The arm is involved; the photo was captured at a distance:
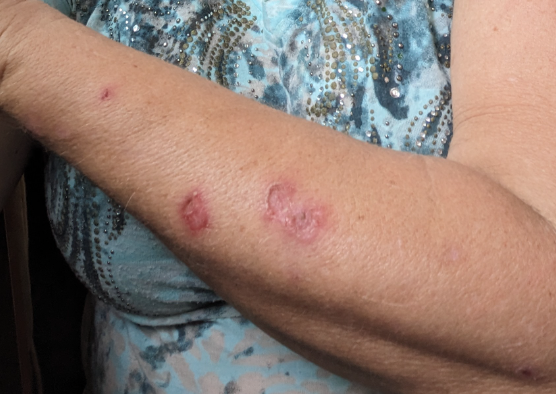The reviewing clinician's impression was: most likely Lichen Simplex Chronicus; also consider Skin infection.